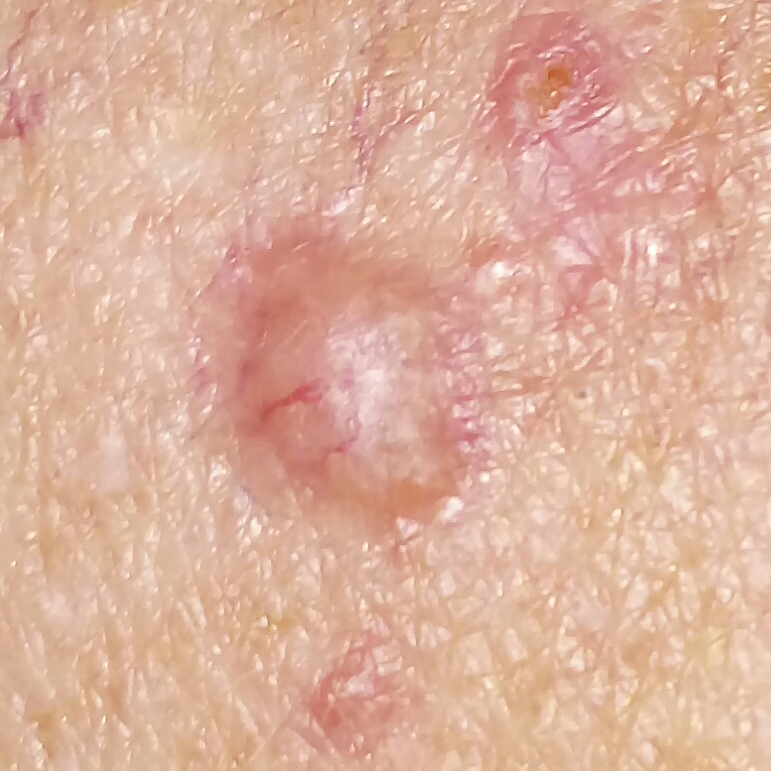Histopathology confirmed a basal cell carcinoma.